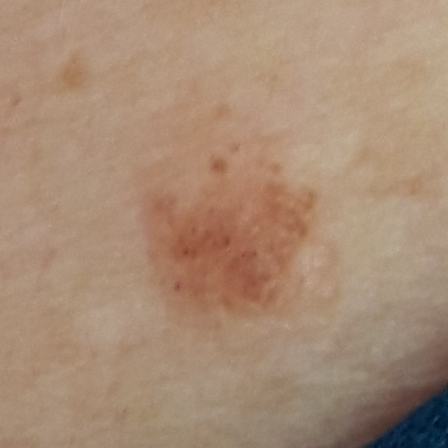Summary: The patient is Fitzpatrick skin type III. A female patient in their 60s. By history, prior skin cancer (patient or family) and prior malignancy (patient or family). A clinical photograph of a skin lesion. Located on the chest. The lesion is roughly 5 by 4 mm. The patient describes that the lesion is elevated, but has not bled and does not itch. Conclusion: The clinical impression was a benign skin lesion — a nevus.